Close-up view. The leg is involved:
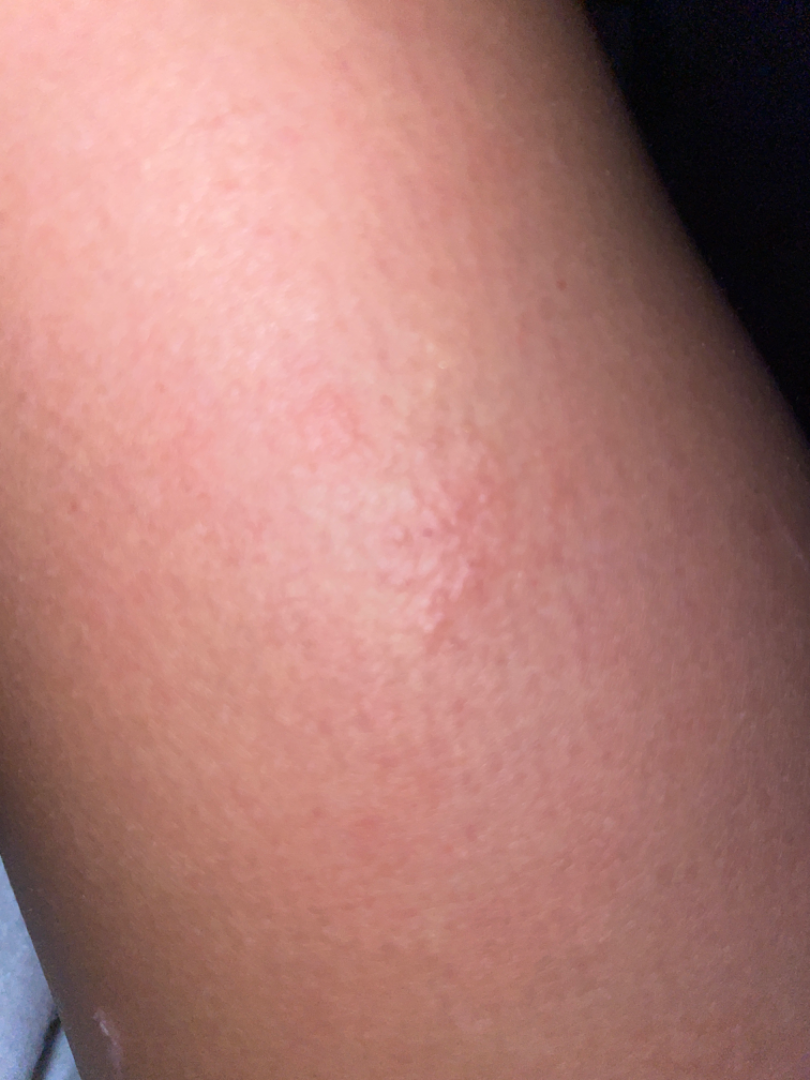The condition has been present for about one day.
Self-categorized by the patient as a rash.
The lesion is described as raised or bumpy.
The patient did not report lesion symptoms.
Reviewed remotely by one dermatologist: the favored diagnosis is Allergic Contact Dermatitis; possibly Eczema.